The contributor reports the lesion is raised or bumpy, rough or flaky and fluid-filled. Reported lesion symptoms include pain, burning and itching. The contributor is 40–49, female. This image was taken at an angle. The lesion involves the back of the hand. The condition has been present for one to three months: 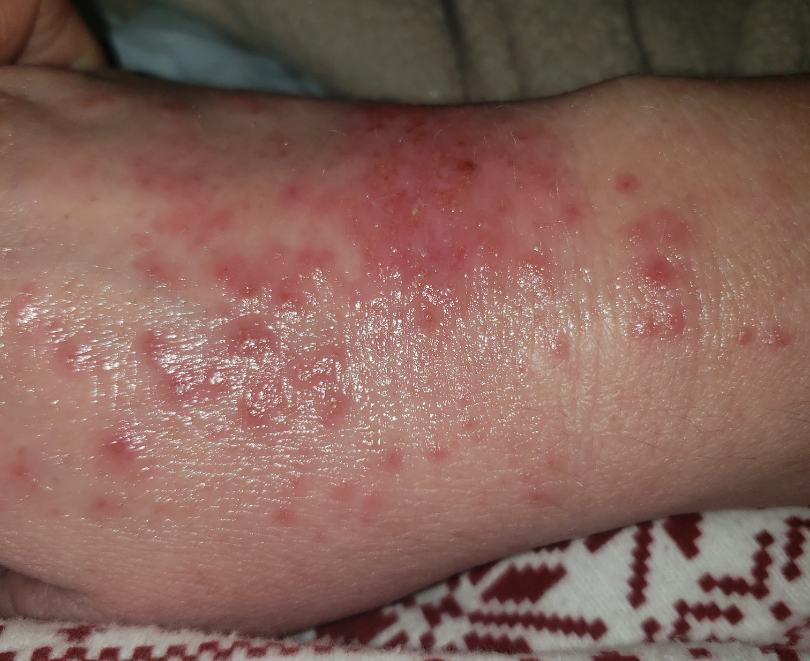The reviewing dermatologist's impression was: Allergic Contact Dermatitis (0.41); Herpes Simplex (0.41); Infected eczema (0.18).